The subject is a female aged 18–29. Reported duration is one to three months. This image was taken at a distance. The lesion is described as raised or bumpy. The patient described the issue as a rash. Located on the leg: 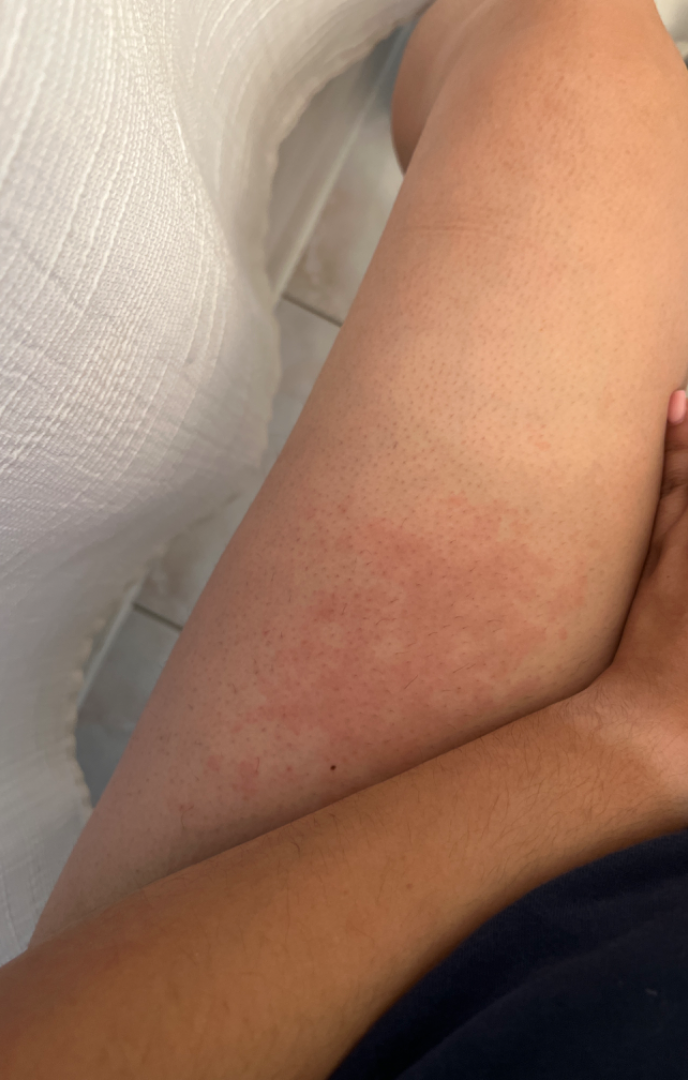On remote dermatologist review, most consistent with Urticaria.